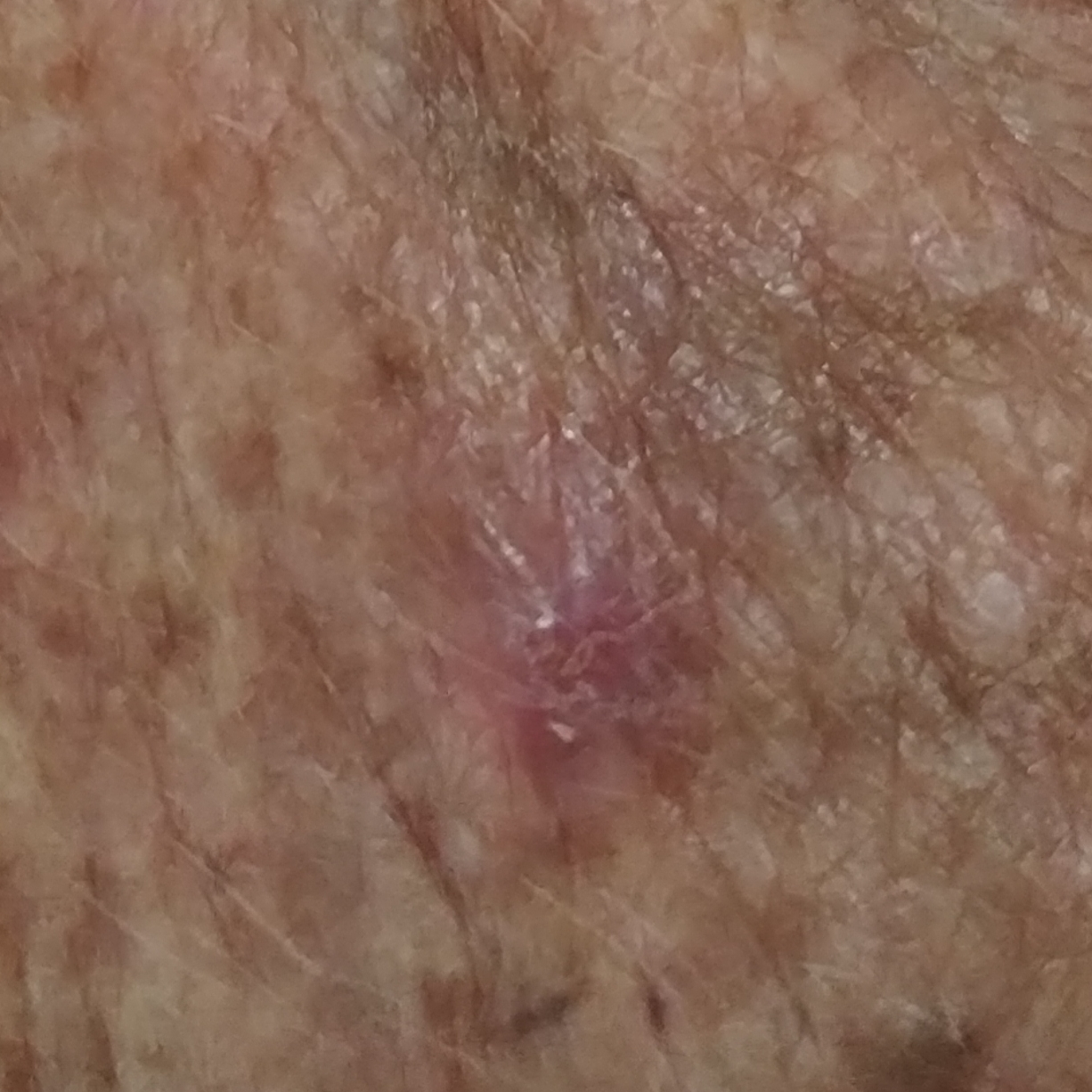| field | value |
|---|---|
| impression | actinic keratosis (clinical consensus) |